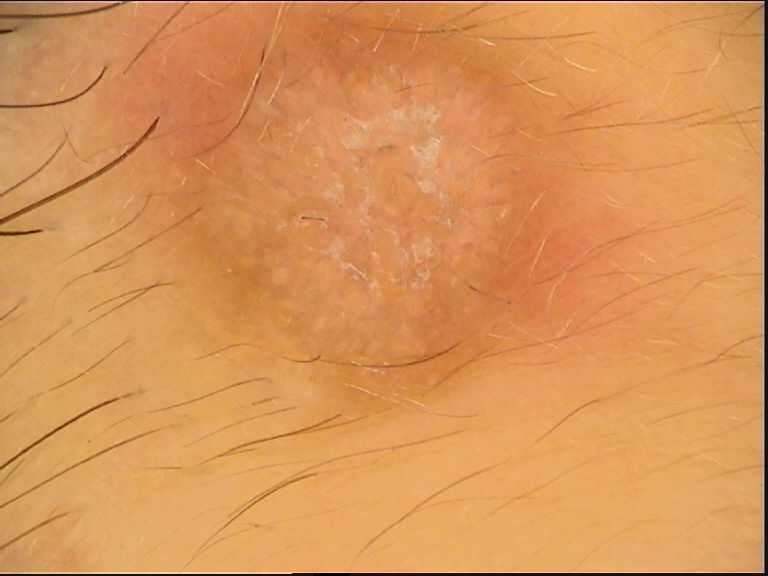Q: What is the diagnosis?
A: dermatofibroma (expert consensus)